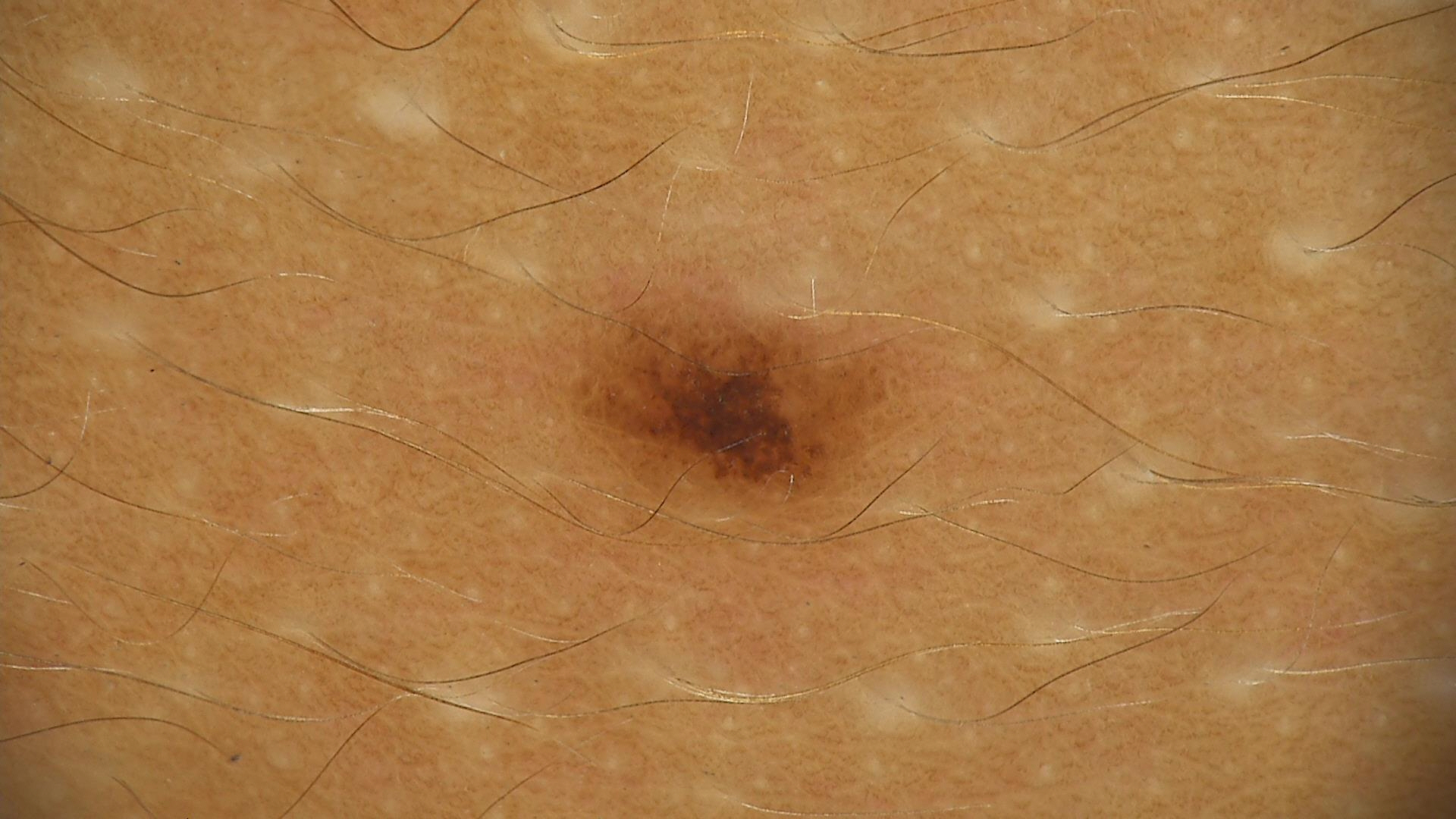A dermoscopic close-up of a skin lesion.
Diagnosed as a benign lesion — a dysplastic junctional nevus.